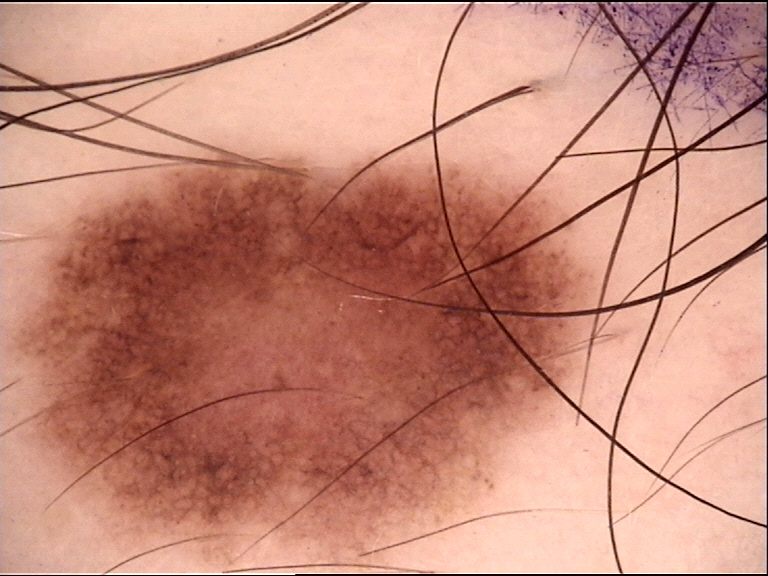<dermoscopy>
<image>dermatoscopy</image>
<diagnosis>
<name>dysplastic junctional nevus</name>
<code>jd</code>
<malignancy>benign</malignancy>
<super_class>melanocytic</super_class>
<confirmation>expert consensus</confirmation>
</diagnosis>
</dermoscopy>